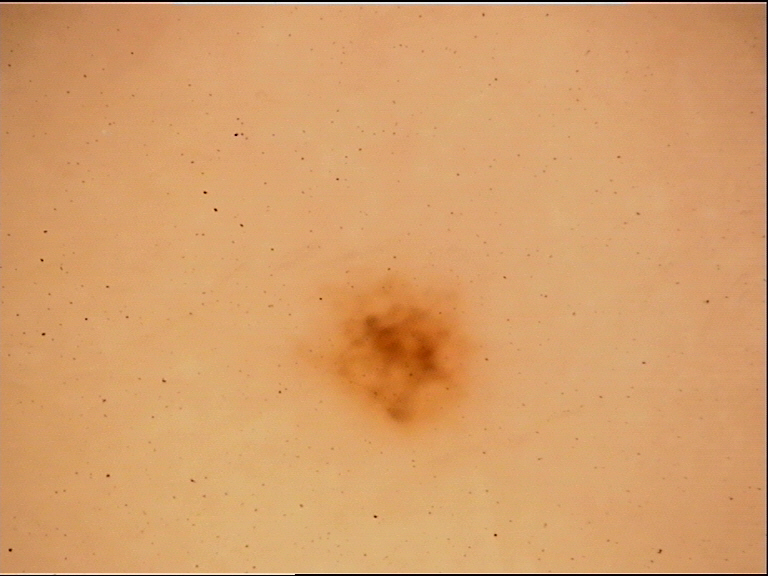The diagnostic label was an acral junctional nevus.